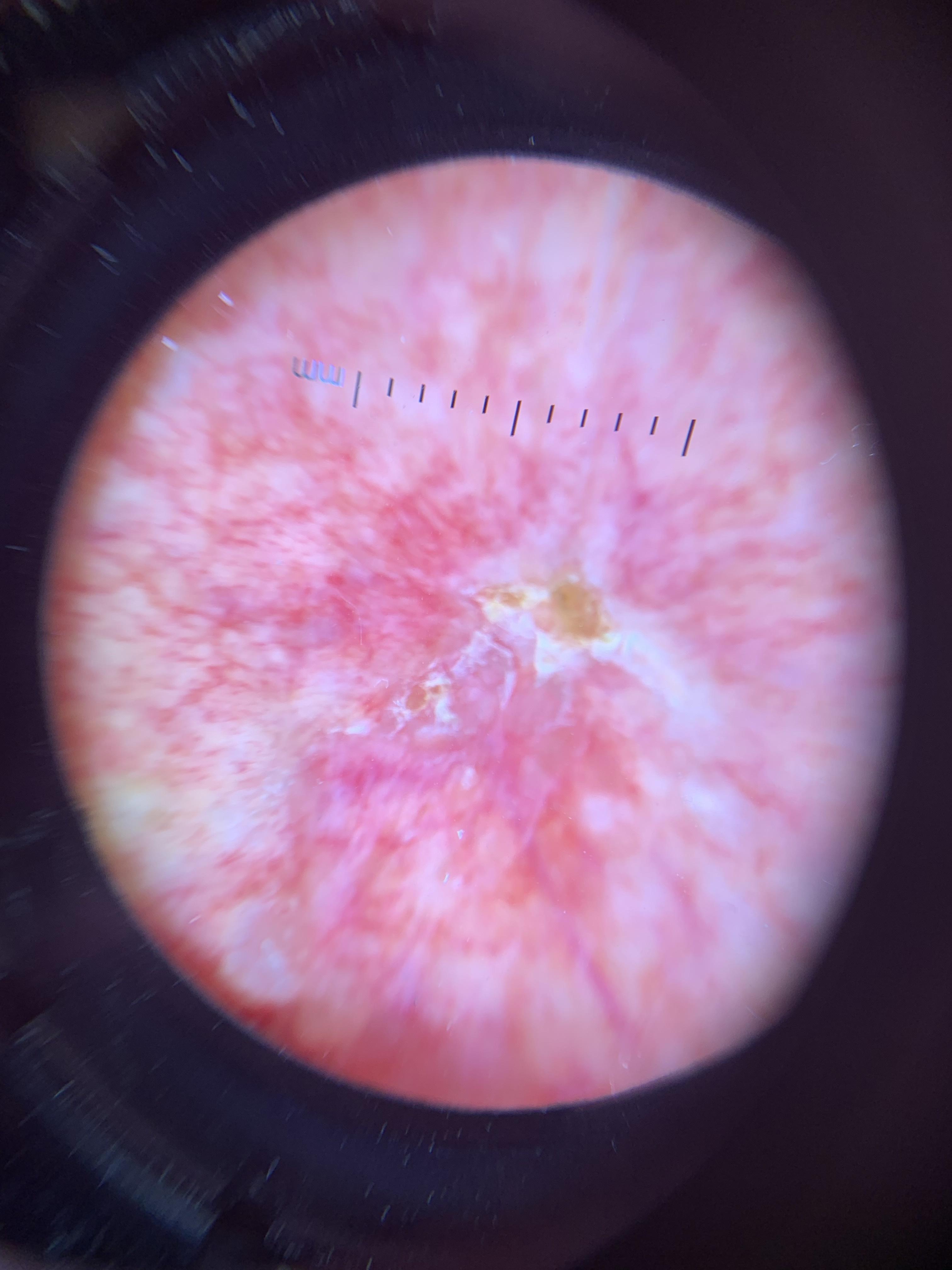diagnostic label: Squamous cell carcinoma (biopsy-proven)